Recorded as Fitzpatrick II. A male patient aged 63 to 67. A contact-polarized dermoscopy image of a skin lesion.
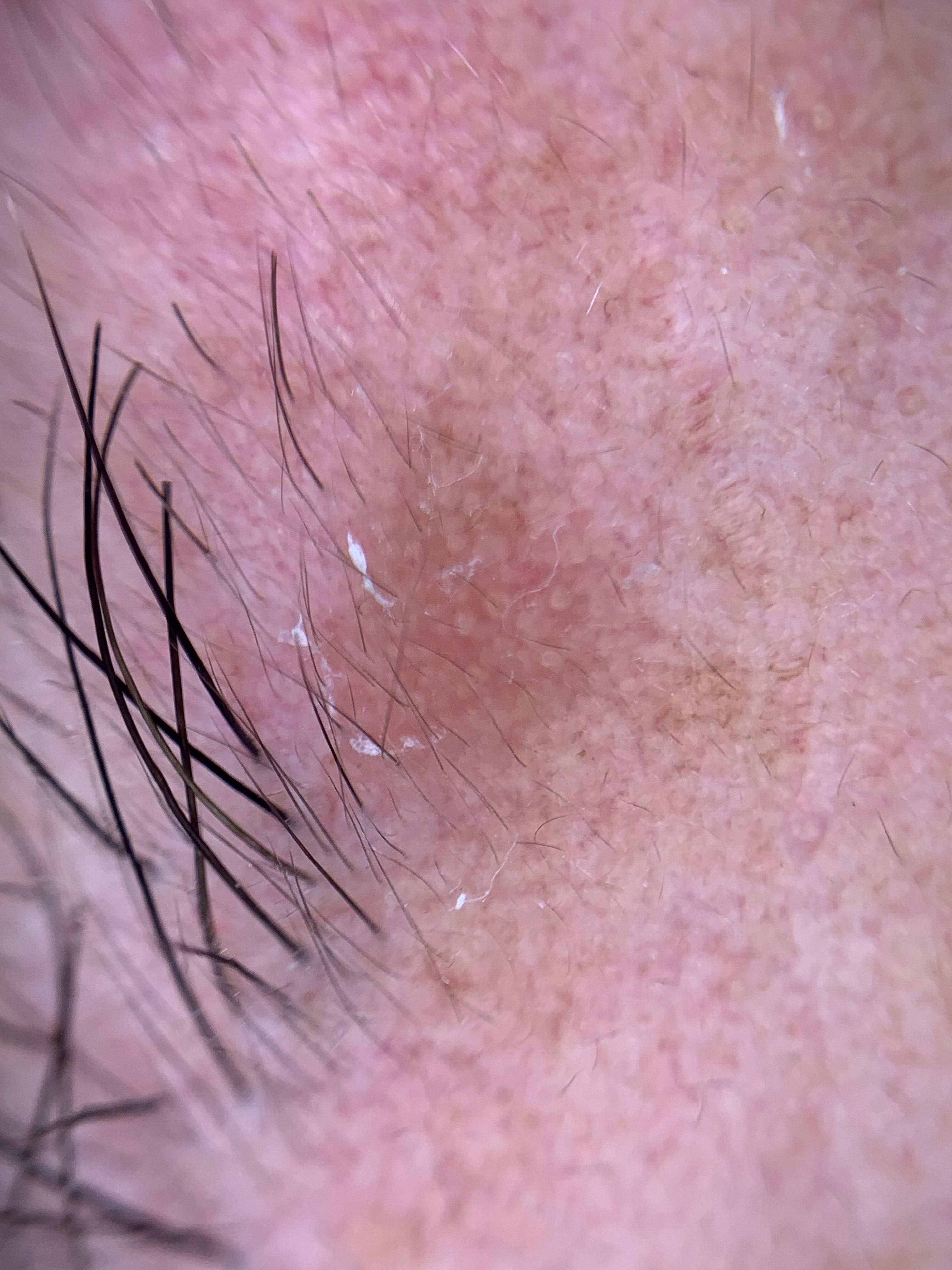Findings:
The lesion involves the head or neck.
Impression:
Clinically diagnosed as a solar or actinic keratosis.